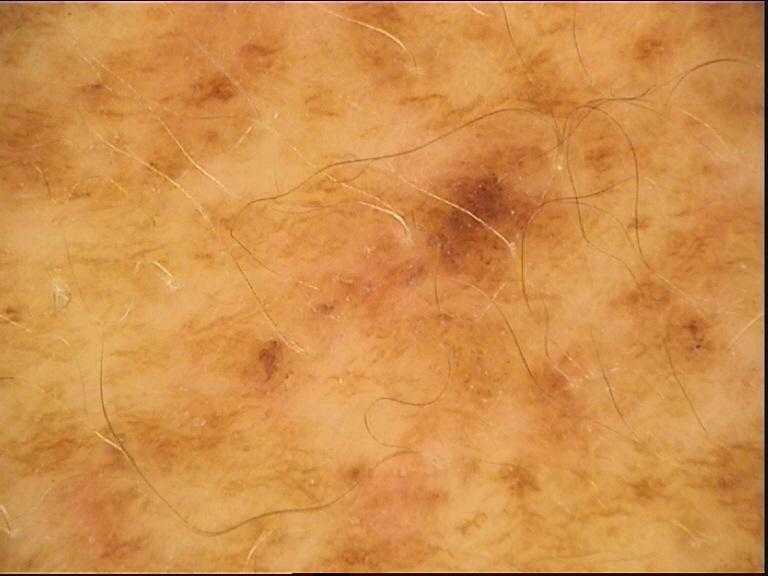The diagnostic label was a banal lesion — a congenital junctional nevus.